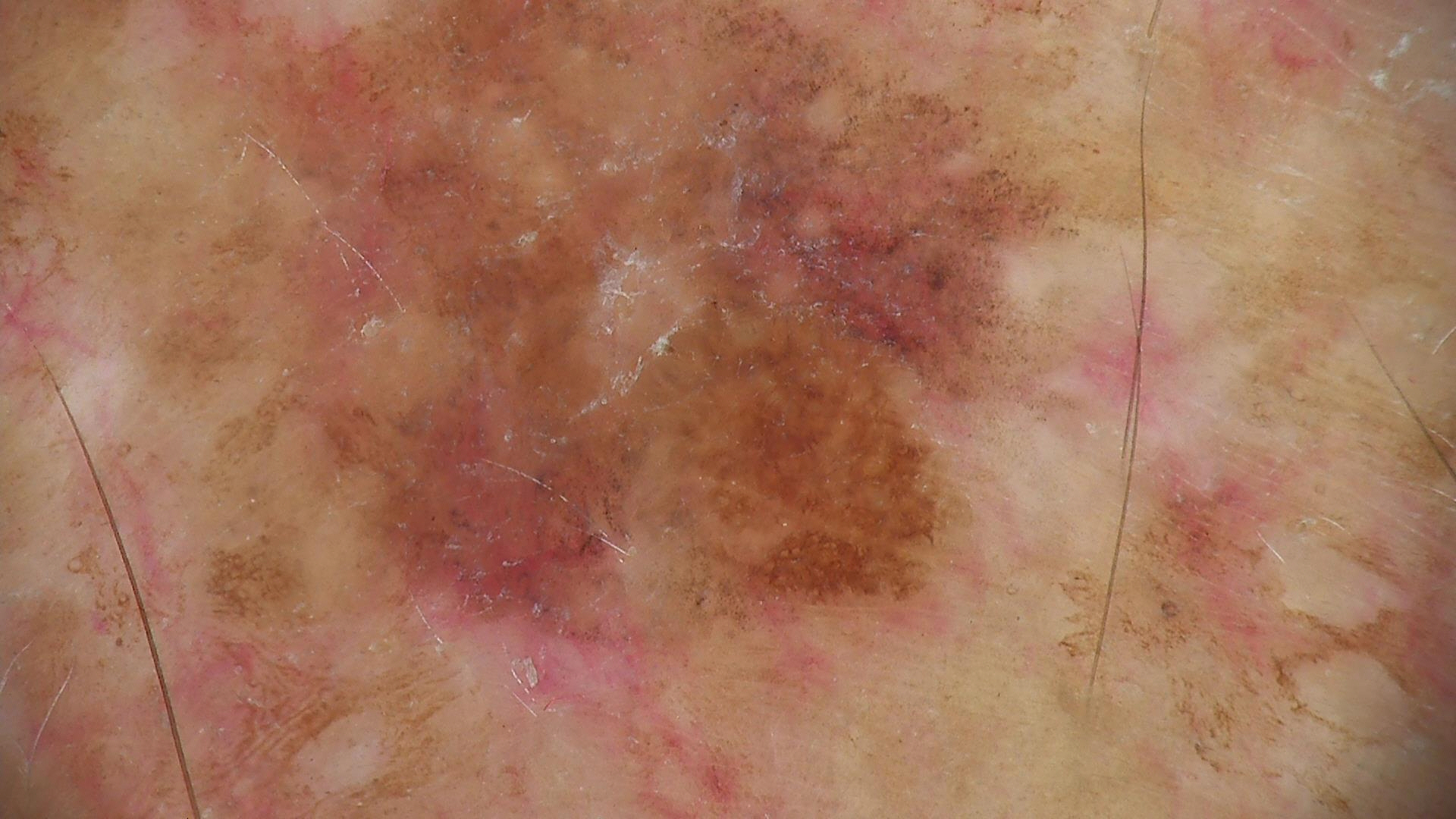Consistent with a seborrheic keratosis.